A smartphone photograph of a skin lesion. The patient was assessed as skin type II. A male patient age 65. By history, alcohol use, tobacco use, prior skin cancer (patient or family), pesticide exposure, and prior malignancy (patient or family):
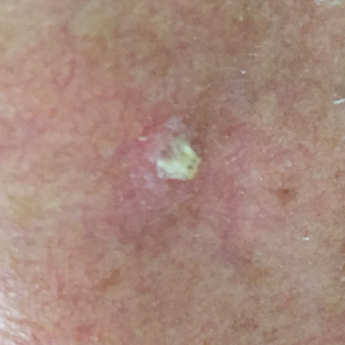| field | value |
|---|---|
| body site | the face |
| diameter | 6 × 5 mm |
| symptoms | elevation, itching, growth / no bleeding, no pain |
| pathology | actinic keratosis (biopsy-proven) |